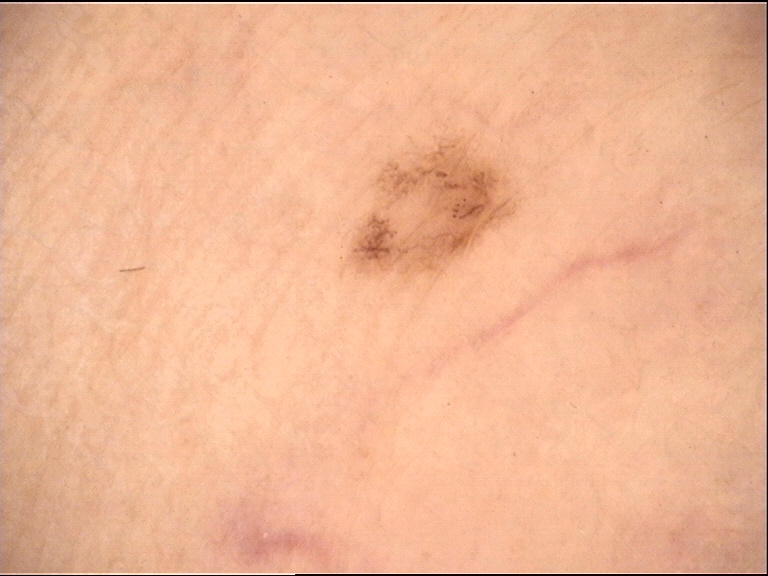Impression: The diagnostic label was an acral dysplastic junctional nevus.